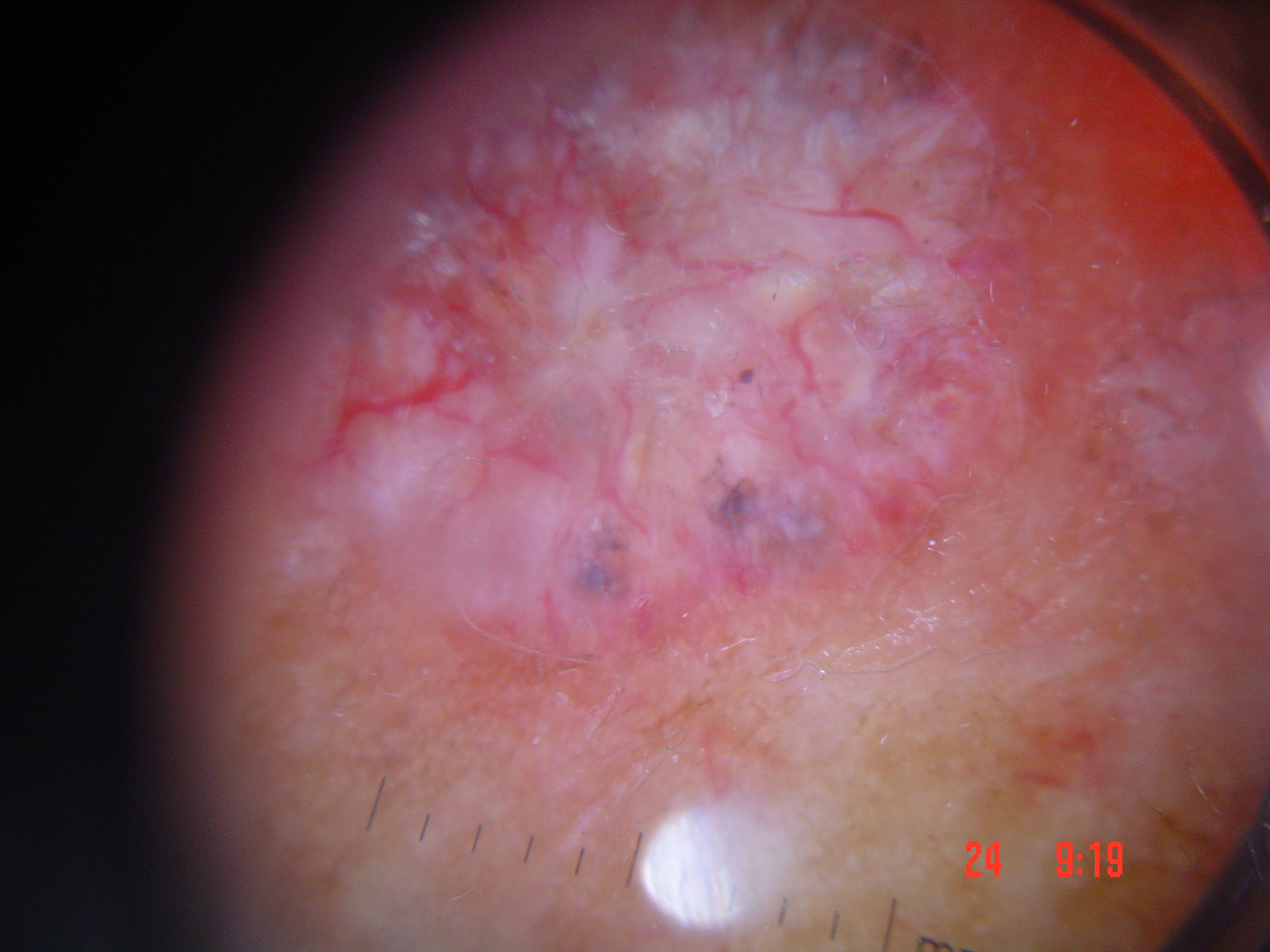Findings:
* modality — dermatoscopy
* category — keratinocytic
* label — basal cell carcinoma (biopsy-proven)